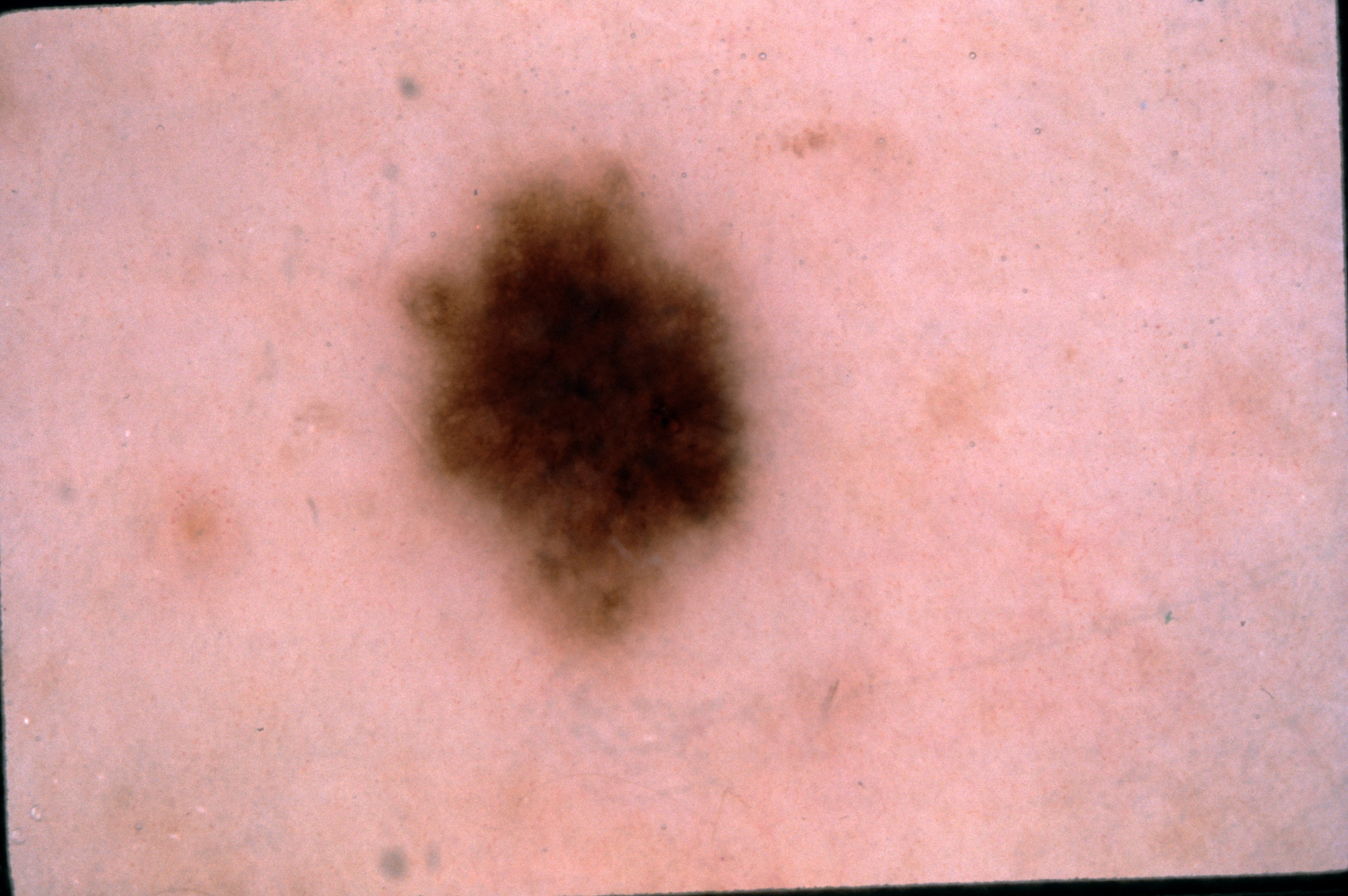| feature | finding |
|---|---|
| subject | male, in their mid- to late 50s |
| image type | dermoscopy of a skin lesion |
| extent | moderate |
| dermoscopic findings | pigment network; absent: streaks, milia-like cysts, and negative network |
| location | bbox=[395, 158, 774, 658] |
| diagnosis | a melanocytic nevus, a benign lesion |